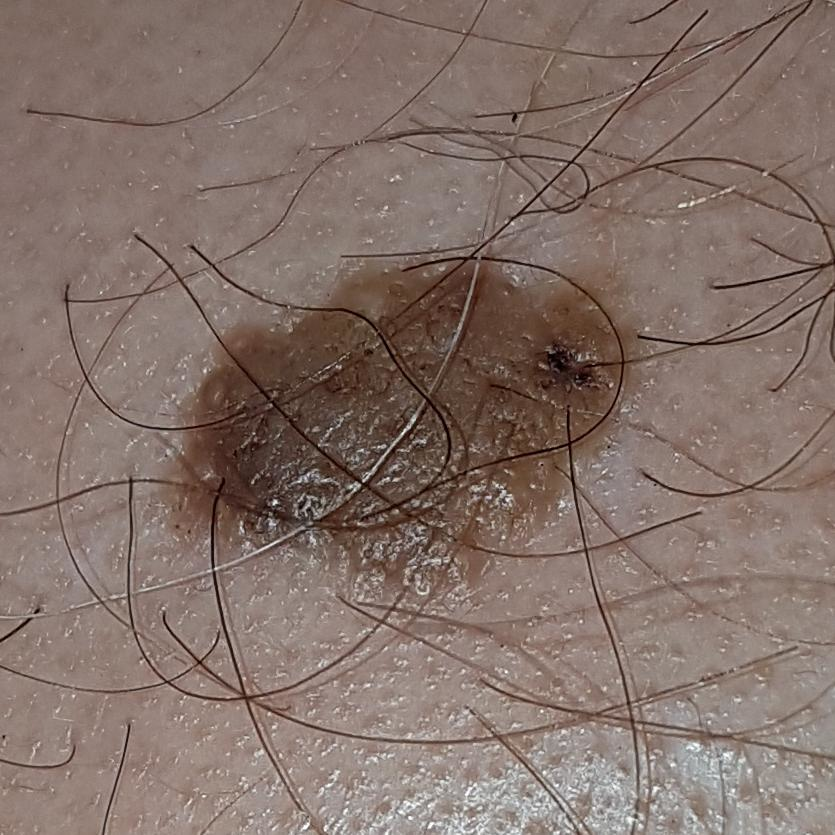A clinical photo of a skin lesion taken with a smartphone. The patient reports that the lesion has grown and is elevated, but has not bled and has not changed. The consensus clinical diagnosis was a nevus.